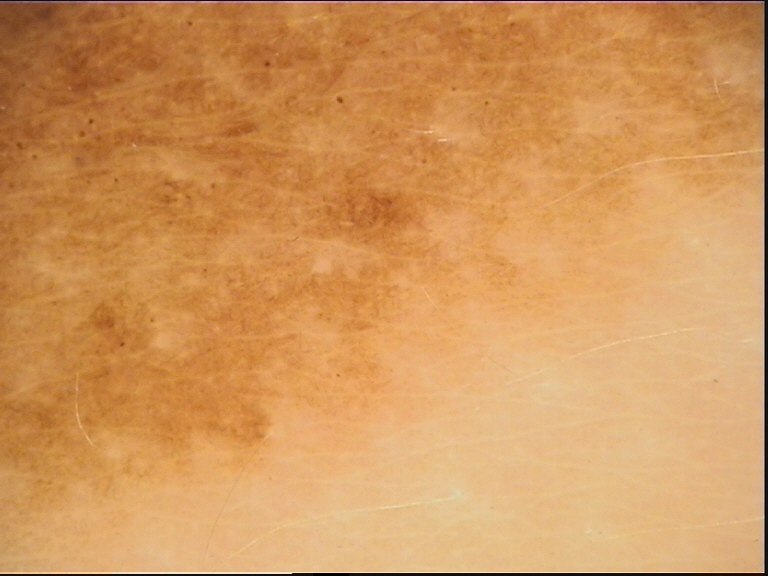{"image": "dermoscopy", "diagnosis": {"name": "congenital junctional nevus", "code": "cjb", "malignancy": "benign", "super_class": "melanocytic", "confirmation": "expert consensus"}}